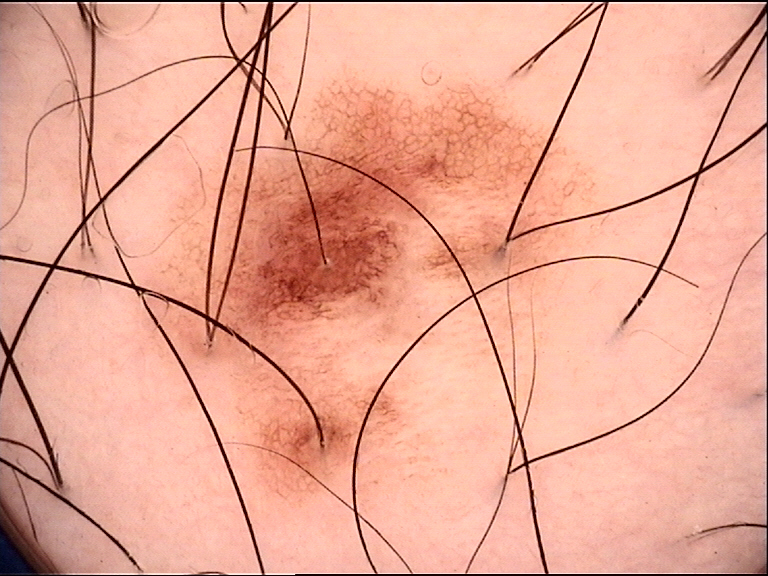assessment — dysplastic junctional nevus (expert consensus).